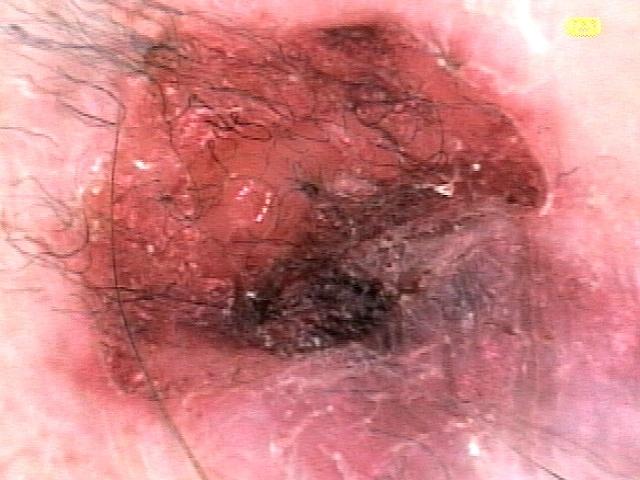Per the chart, a prior melanoma. A dermatoscopic image of a skin lesion. The patient is Fitzpatrick phototype II. A male patient aged 83 or older. The lesion is on the trunk. The diagnostic impression was a vascular lesion.